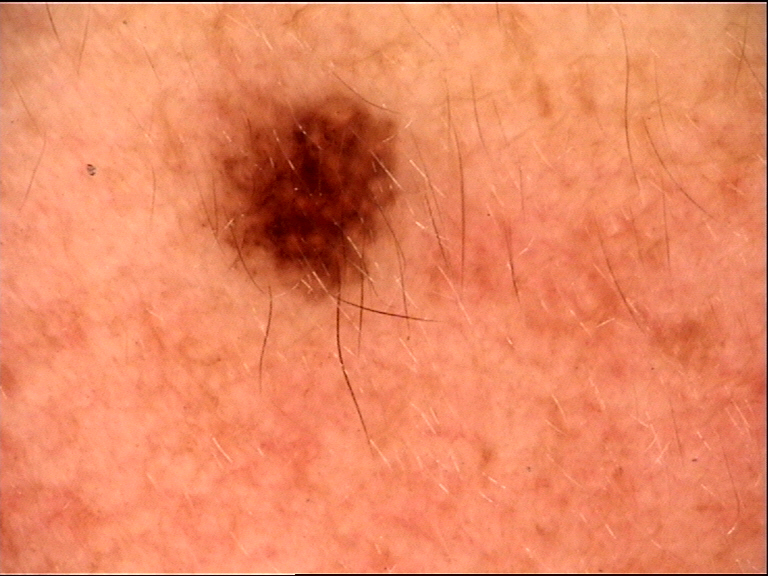The diagnostic label was a dysplastic compound nevus.